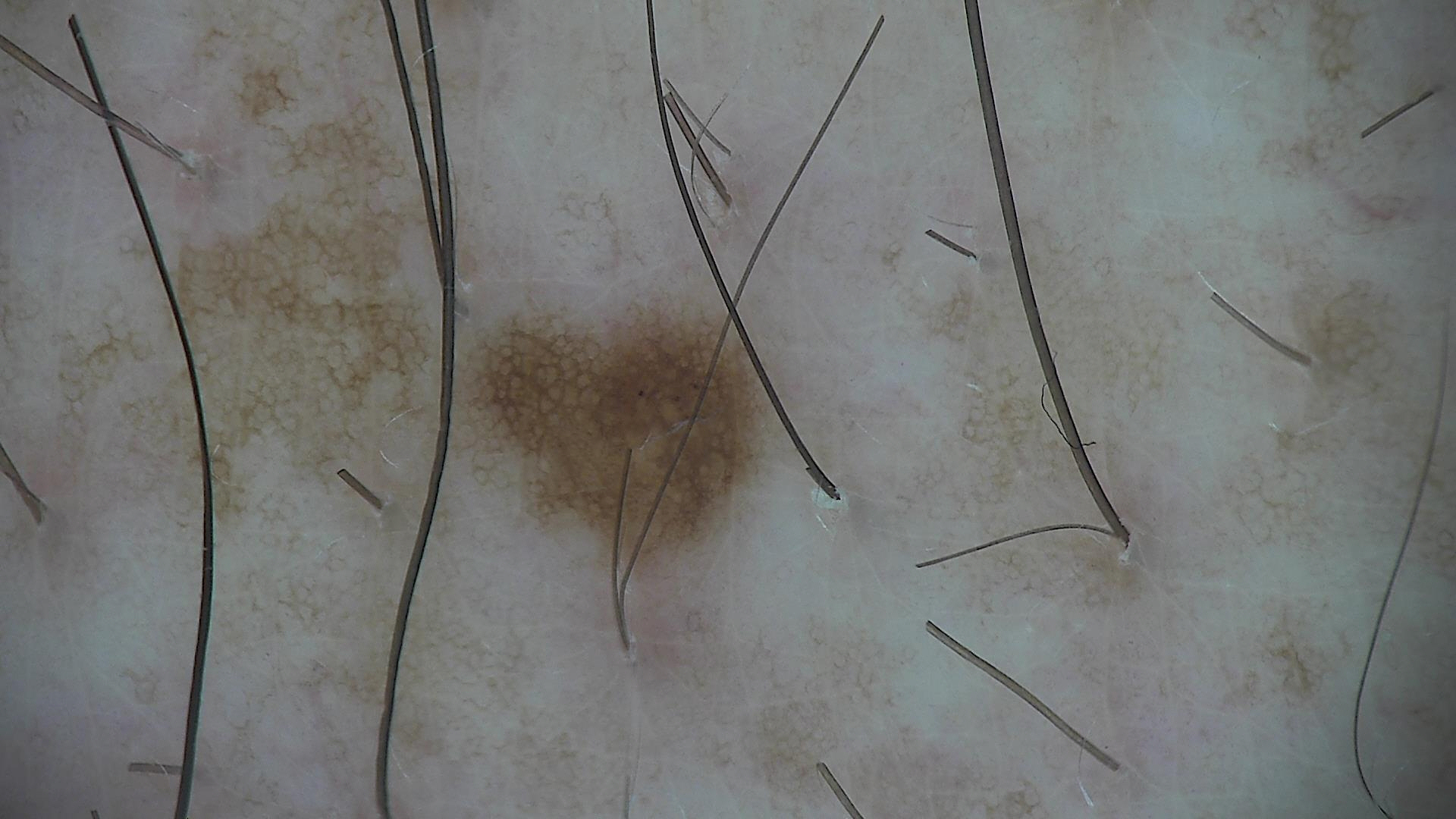Impression: The diagnostic label was a dysplastic junctional nevus.